The contributor reports pain and burning. Female patient, age 18–29. Self-categorized by the patient as a rash. The photograph is a close-up of the affected area. The affected area is the arm. The contributor reports the condition has been present for about one day: 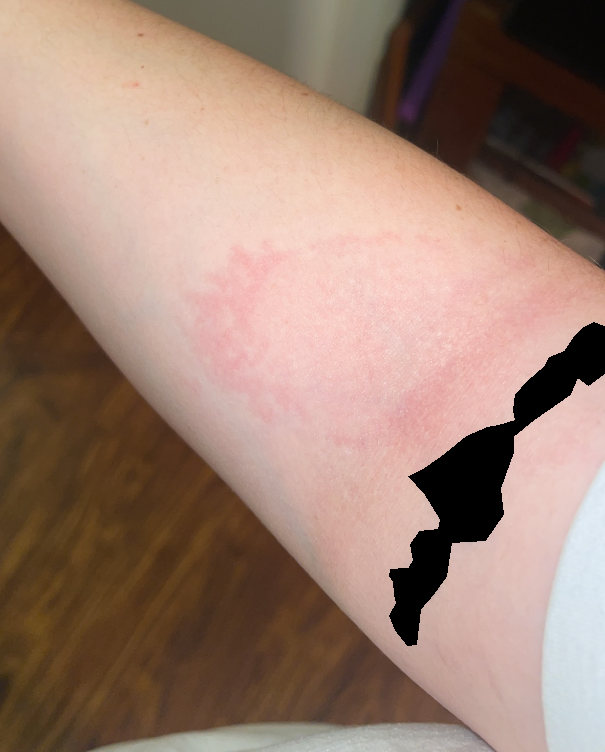Case summary:
* clinical impression · a single dermatologist reviewed the case: the leading consideration is Eczema; also raised was Allergic Contact Dermatitis